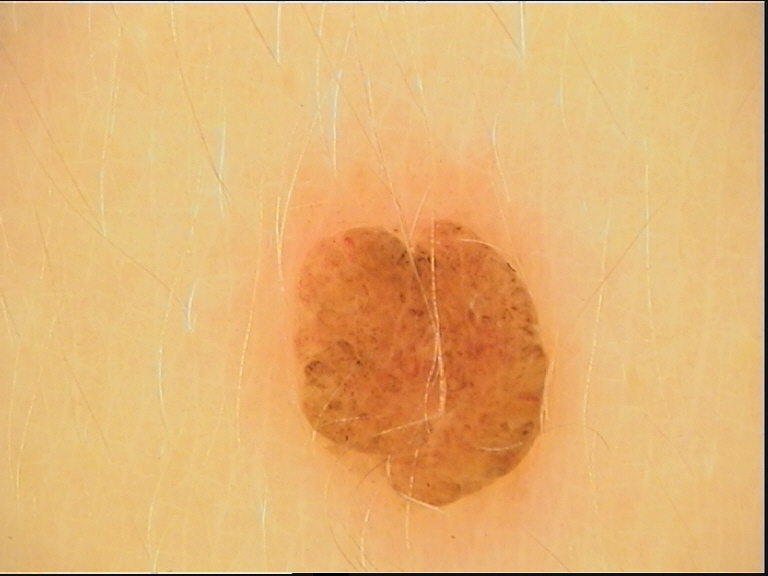Findings:
• classification: banal
• label: dermal nevus (expert consensus)